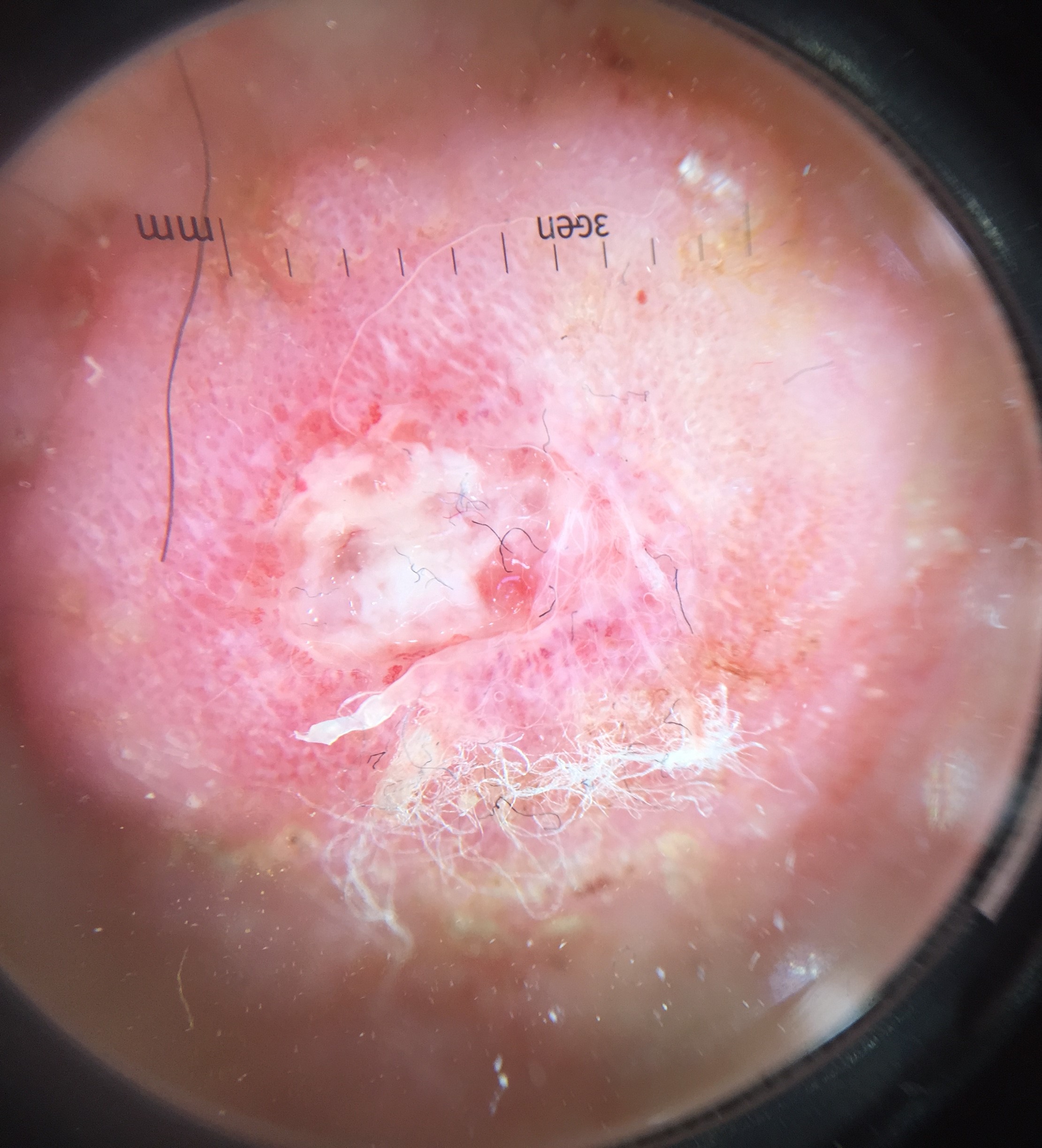diagnostic label — squamous cell carcinoma (biopsy-proven)